Dermoscopy of a skin lesion.
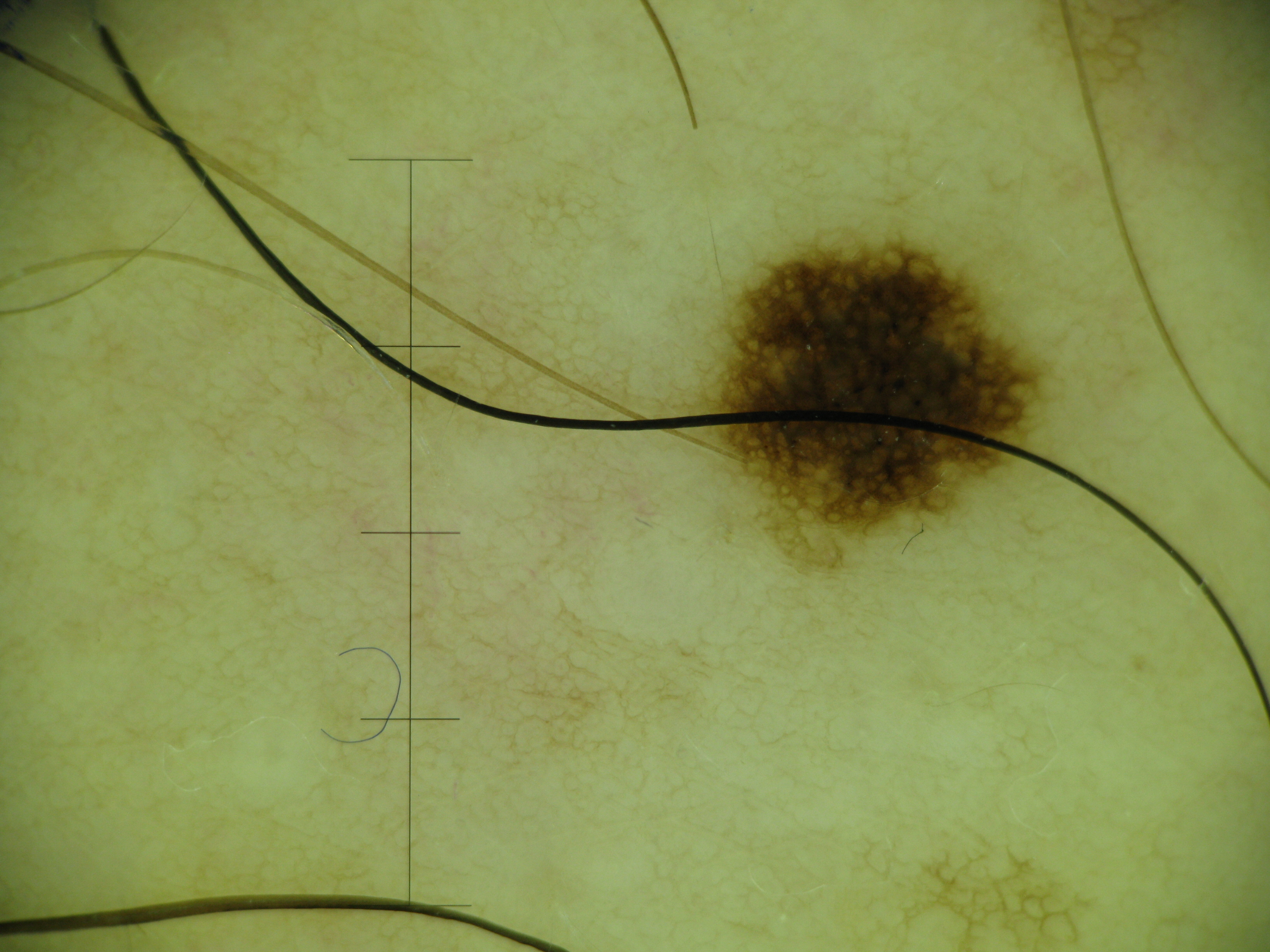diagnostic label = dysplastic junctional nevus (expert consensus).